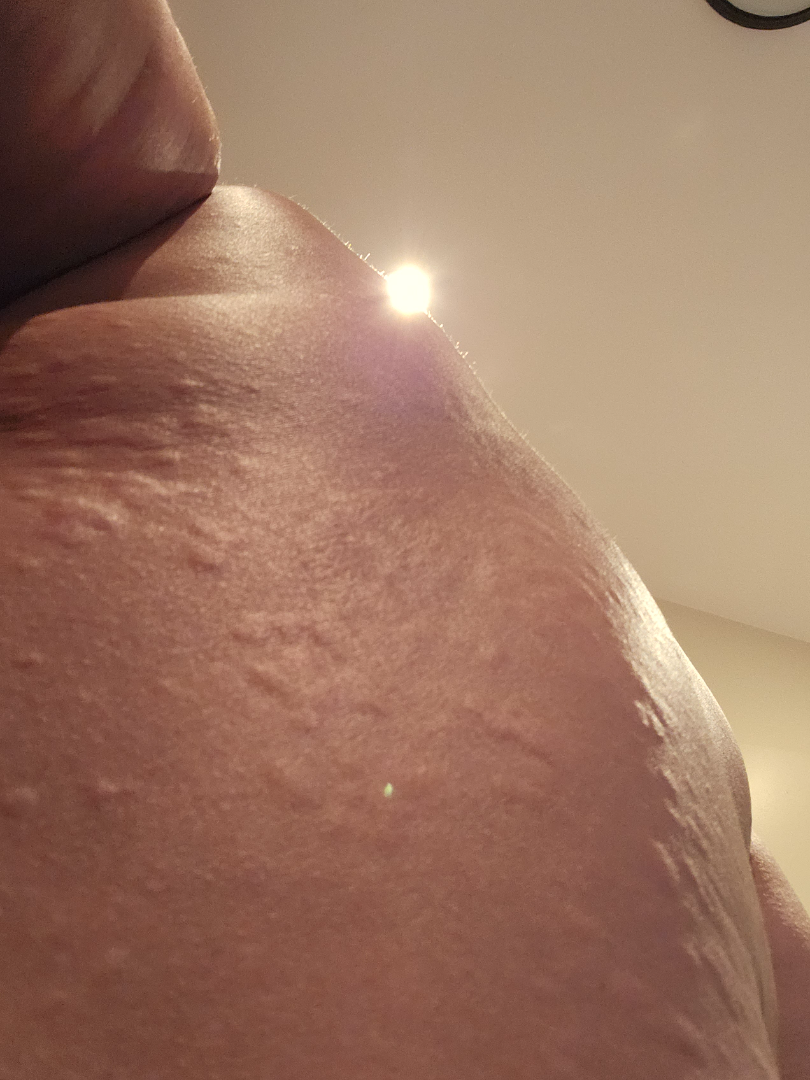Findings:
• assessment: indeterminate
• photo taken: close-up
• self-categorized as: a rash
• site: arm and head or neck